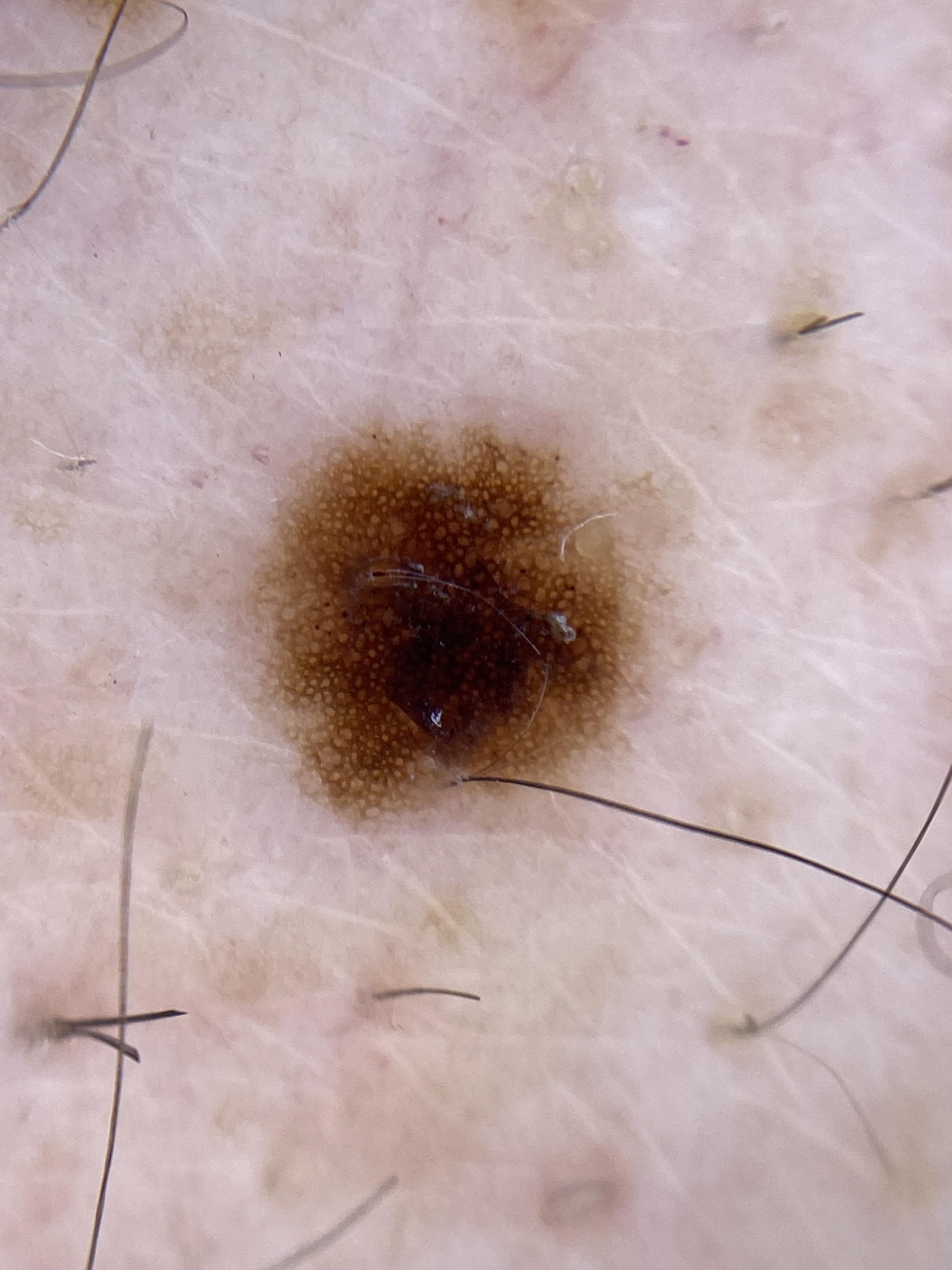{"melanoma_history": {"personal_hx_melanoma": true}, "image": "dermoscopic image", "patient": {"age_approx": 75, "sex": "male"}, "diagnosis": {"name": "Nevus", "malignancy": "benign", "confirmation": "histopathology", "lineage": "melanocytic"}}